The affected area is the arm, head or neck, leg, palm and sole of the foot. The photograph is a close-up of the affected area. The contributor is a female aged 18–29:
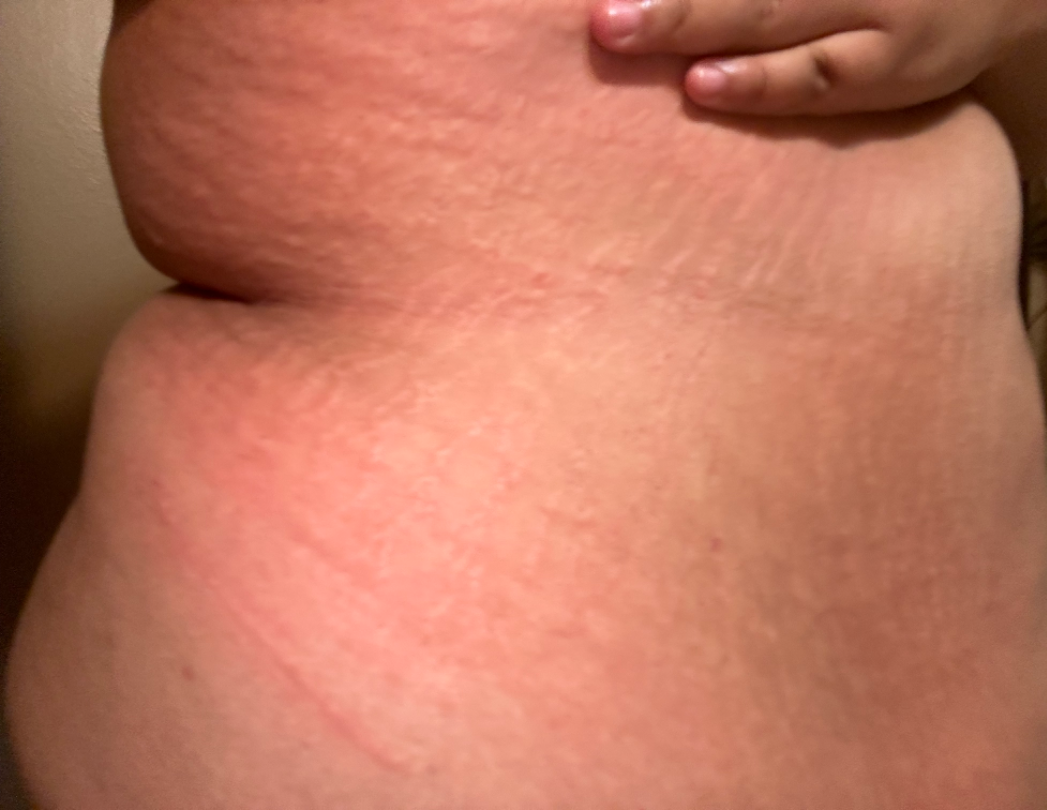Notes:
- differential — the primary impression is Urticaria; also consider Drug Rash